This image was taken at an angle. Located on the front of the torso.
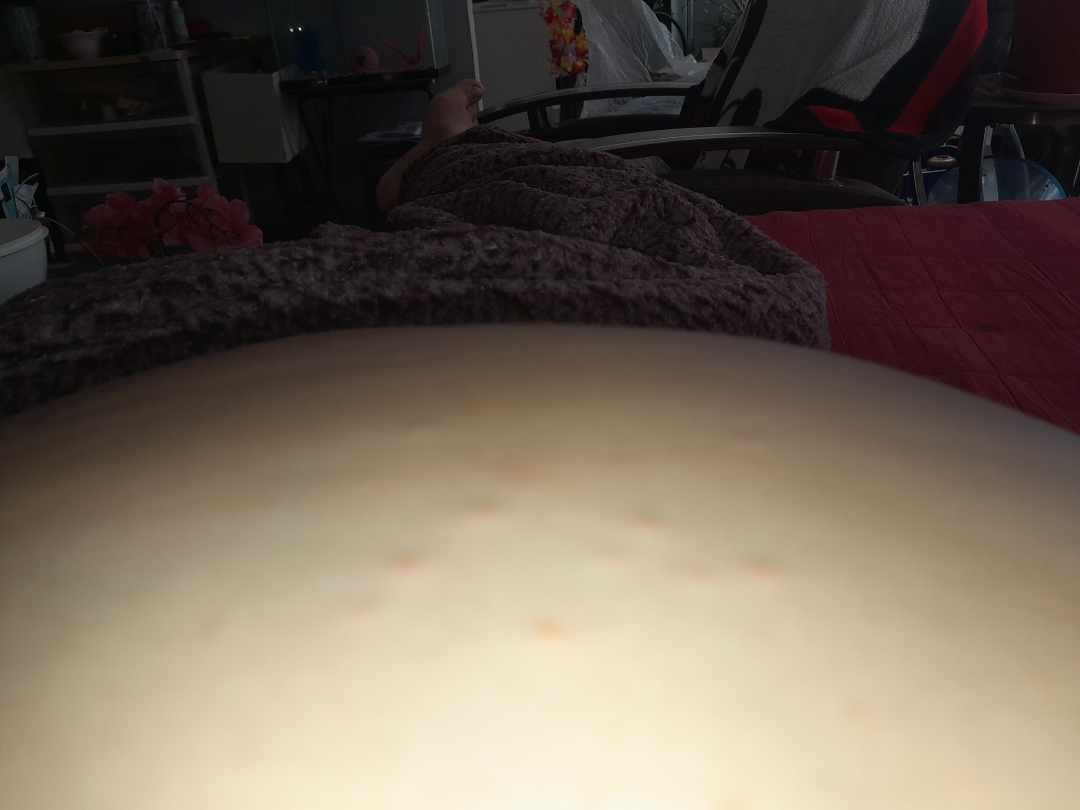History:
Present for less than one week. Associated systemic symptoms include fatigue, joint pain and chills. Skin tone: Fitzpatrick phototype II; non-clinician graders estimated 4 on the Monk skin tone scale. The patient notes bothersome appearance and itching. Self-categorized by the patient as a rash. Texture is reported as fluid-filled and raised or bumpy.
Impression:
The reviewing dermatologists' impression was: Folliculitis (0.41); Molluscum Contagiosum (0.41); Scabies (0.18).